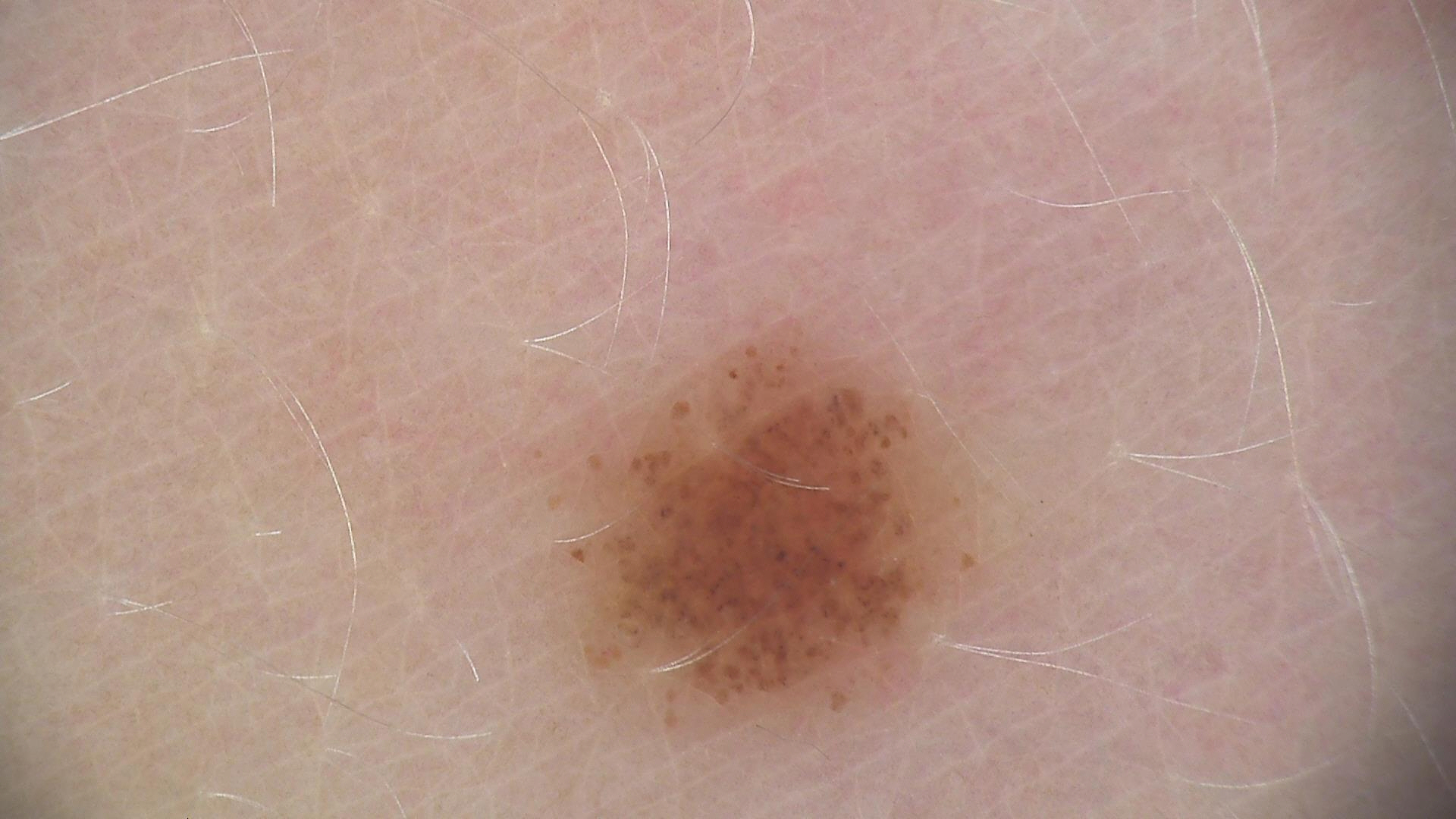Classified as a benign lesion — a dysplastic junctional nevus.